A clinical close-up of a skin lesion · a male patient aged 83 · referred with a clinical suspicion of Bowen's disease.
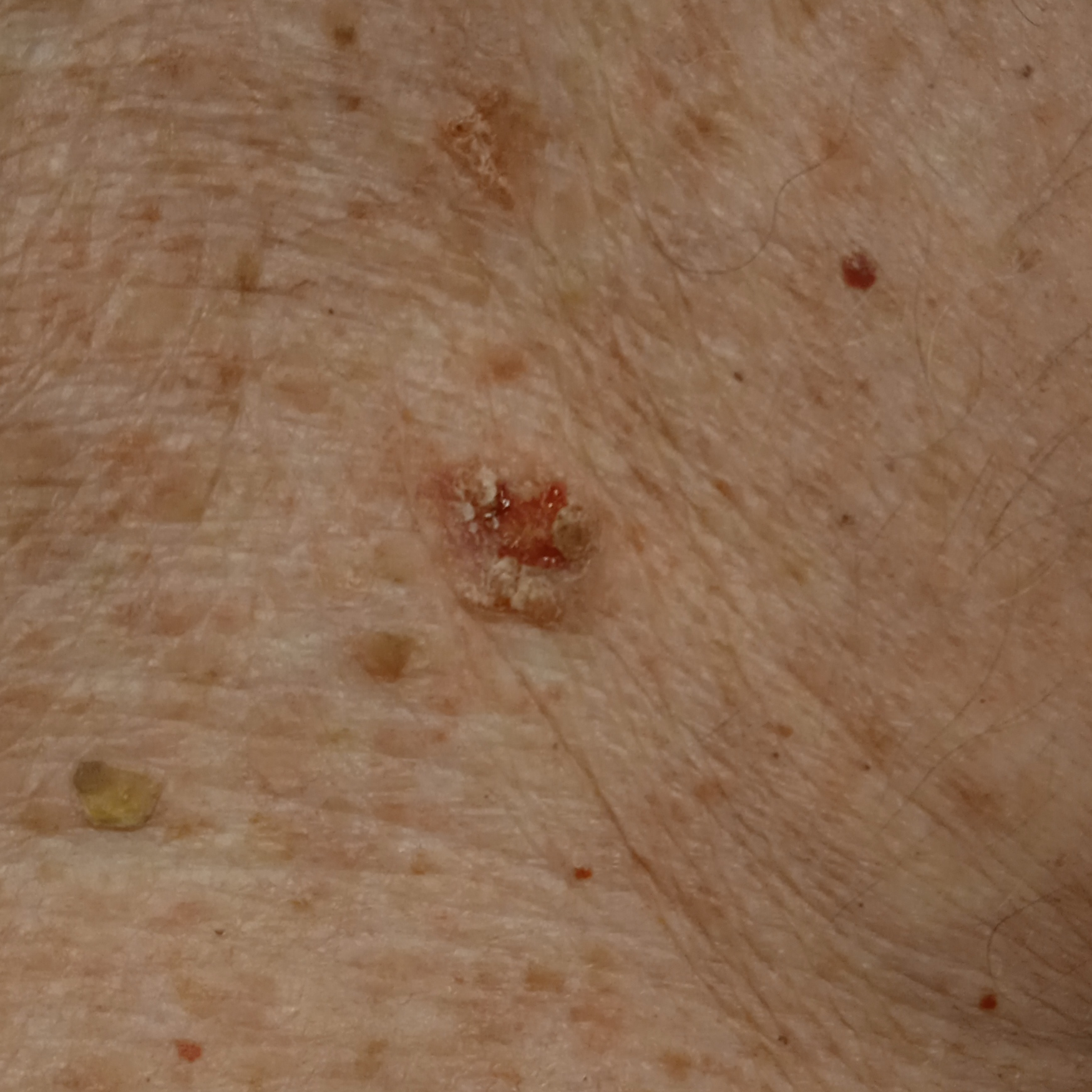site=the torso; diameter=14.5 mm; assessment=squamous cell carcinoma (dermatologist consensus).